A male subject in their mid-80s or older; dermoscopy of a skin lesion — 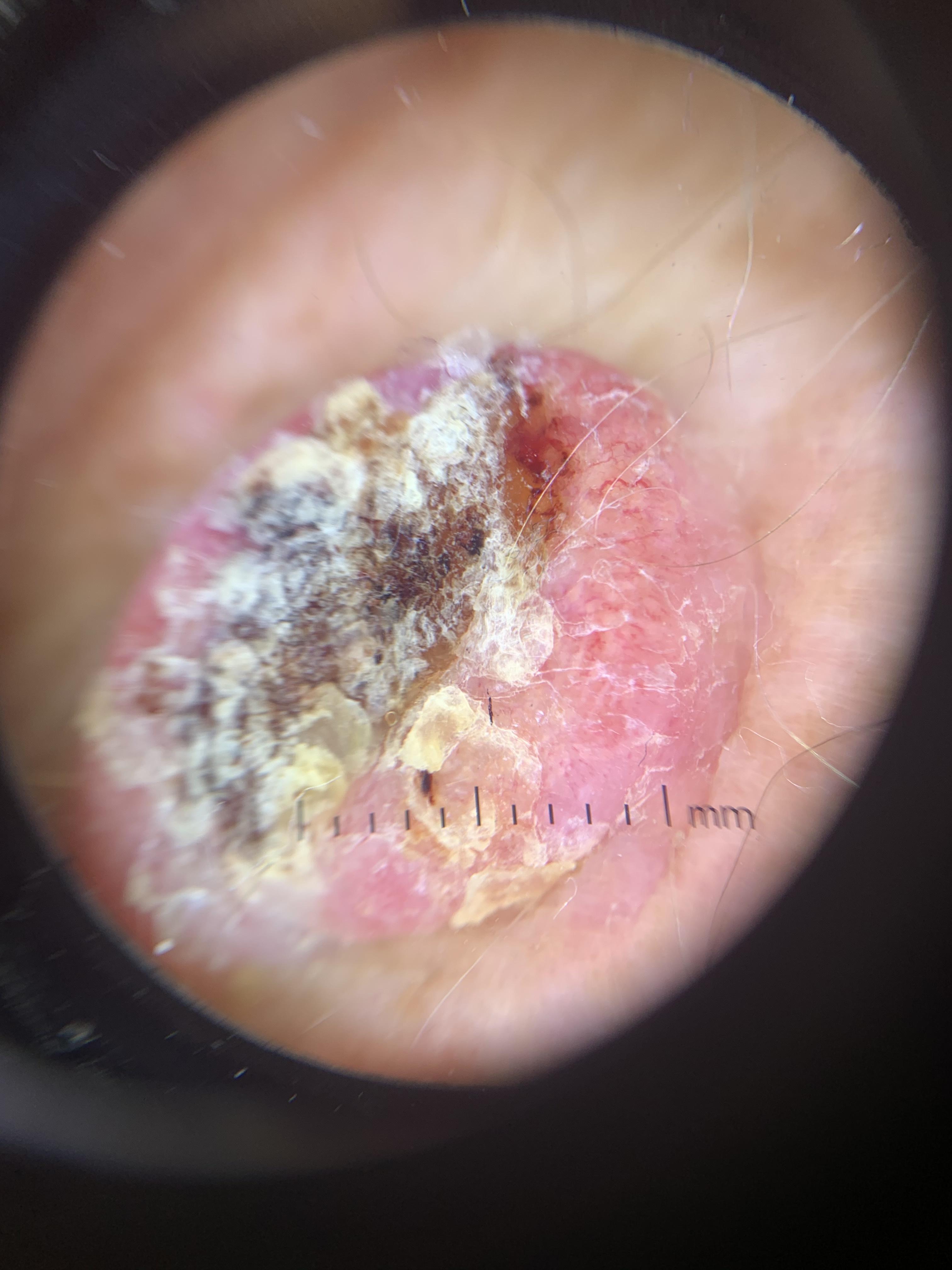{
  "diagnosis": {
    "name": "Squamous cell carcinoma",
    "malignancy": "malignant",
    "confirmation": "histopathology",
    "lineage": "epidermal"
  }
}